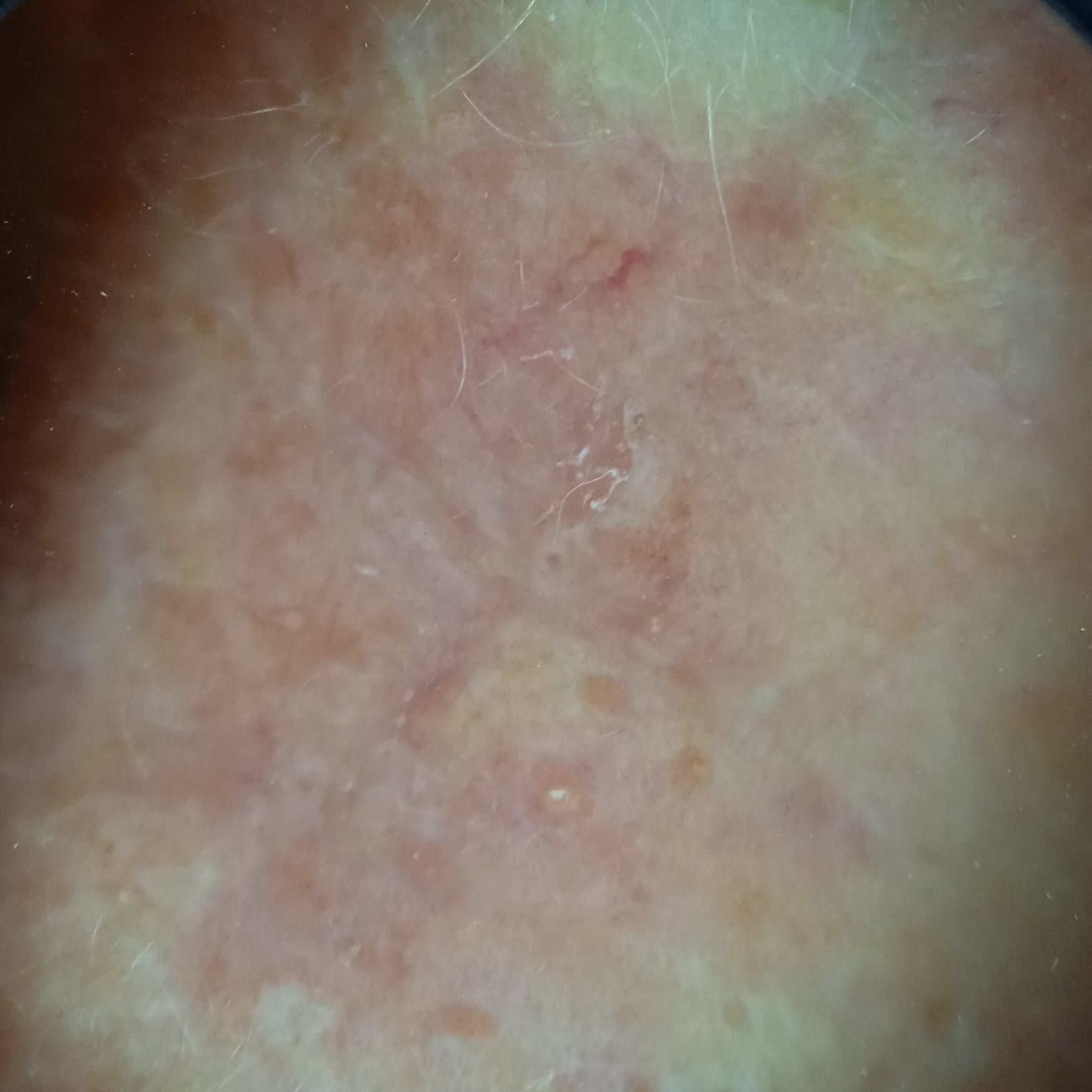<skin_lesion>
<referral>research study (no referral diagnosis)</referral>
<mole_burden>few melanocytic nevi overall</mole_burden>
<sun_reaction>skin tans without first burning</sun_reaction>
<lesion_size>
<diameter_mm>9.9</diameter_mm>
</lesion_size>
<diagnosis>
<name>actinic keratosis</name>
<malignancy>benign</malignancy>
</diagnosis>
</skin_lesion>